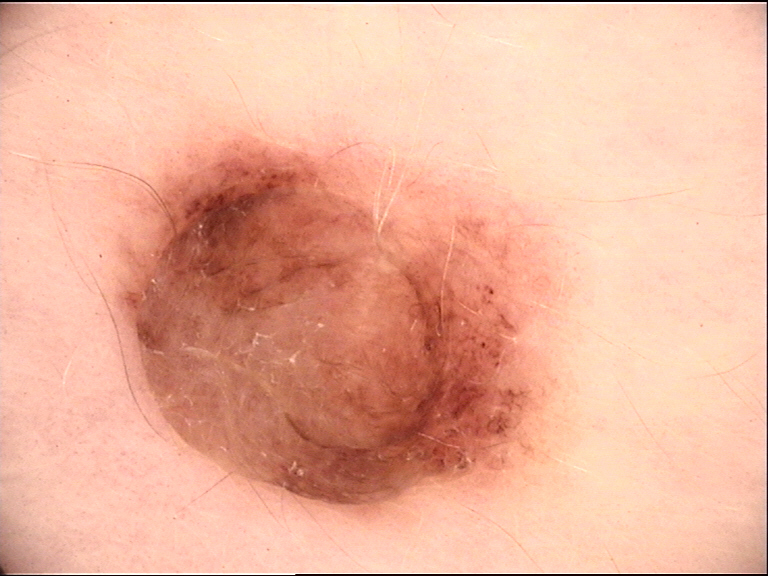A dermoscopic image of a skin lesion.
The morphology is that of a banal lesion.
Labeled as a dermal nevus.